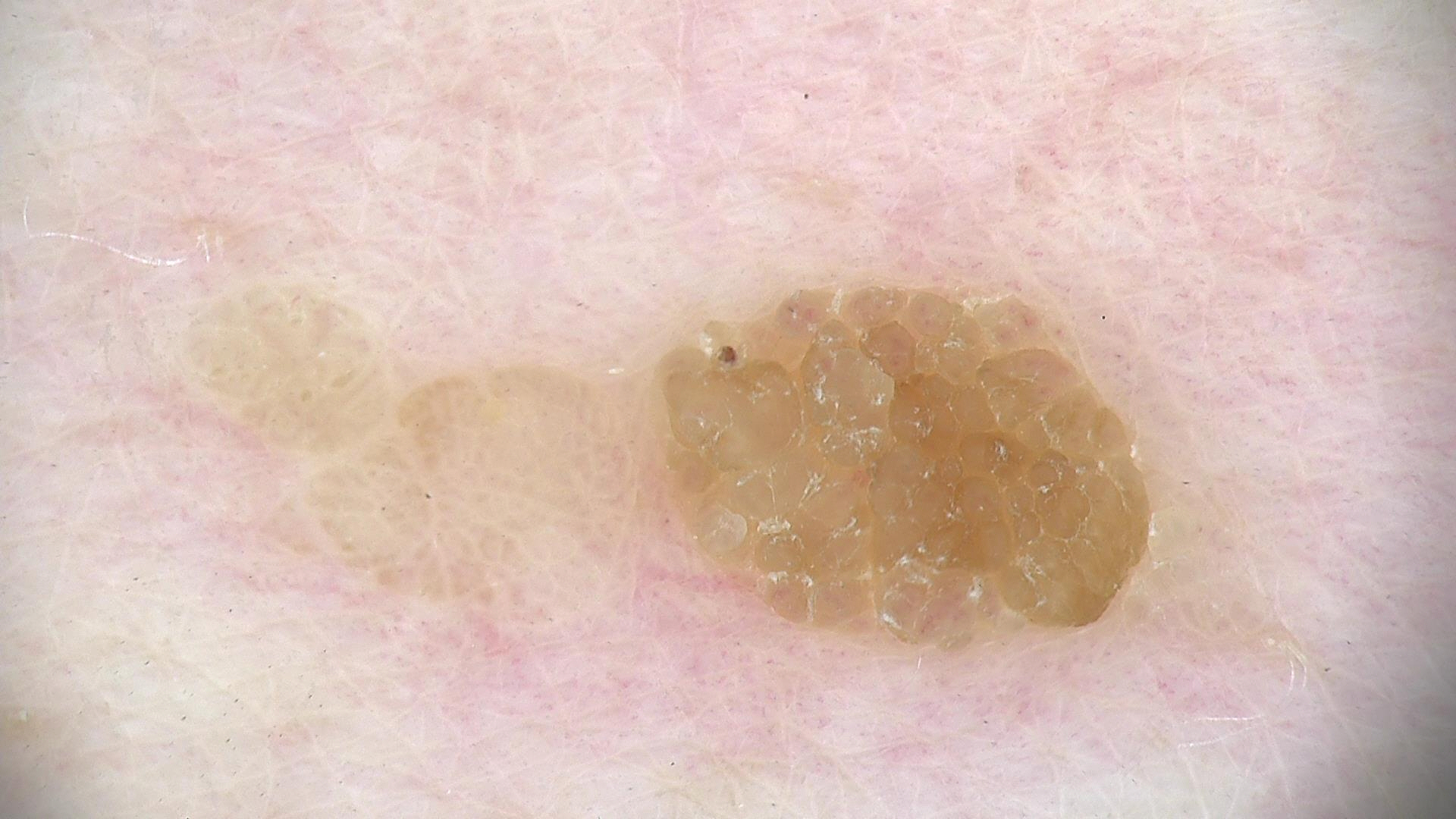This is a keratinocytic lesion. Labeled as a seborrheic keratosis.